Located on the leg · the patient reports the condition has been present for about one day · the lesion is associated with itching · the patient reported no systemic symptoms · this is a close-up image · the subject is a female aged 70–79 · Fitzpatrick phototype I; lay reviewers estimated MST 2 or 3 · texture is reported as raised or bumpy:
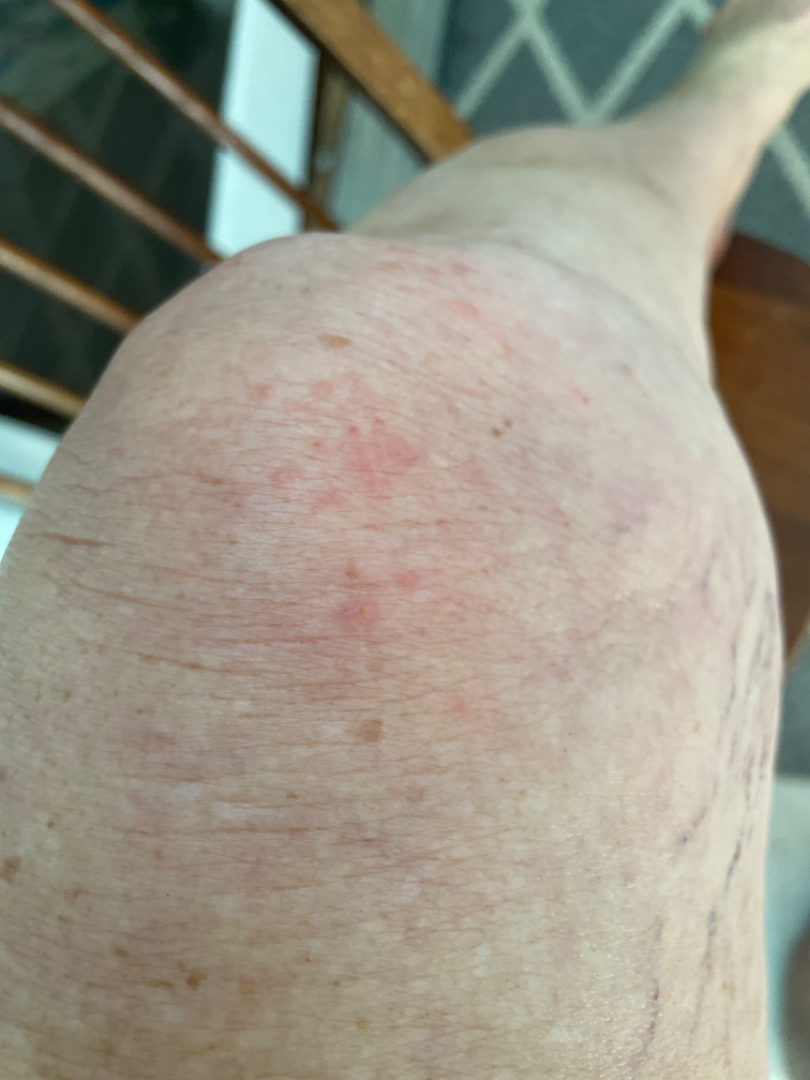On photographic review by a dermatologist, Psoriasis, Eczema and Dermatitis herpetiformis were each considered, in no particular order.